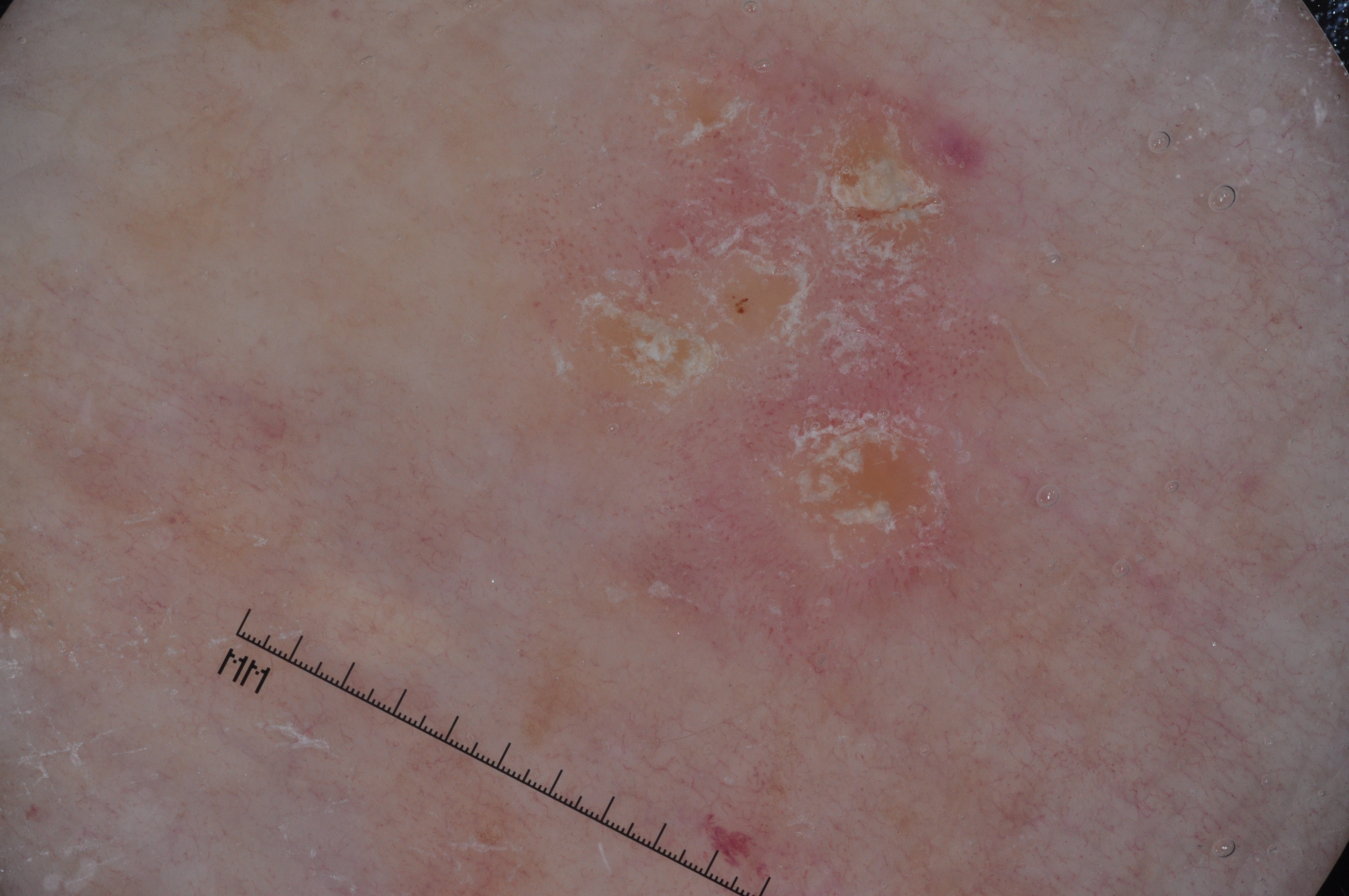Image and clinical context:
A dermoscopic close-up of a skin lesion. The lesion's extent is [504,57,1062,665]. Dermoscopic review identifies no milia-like cysts, negative network, pigment network, or streaks.
Assessment:
Diagnosed as a seborrheic keratosis.